A close-up photograph. Female contributor, age 18–29:
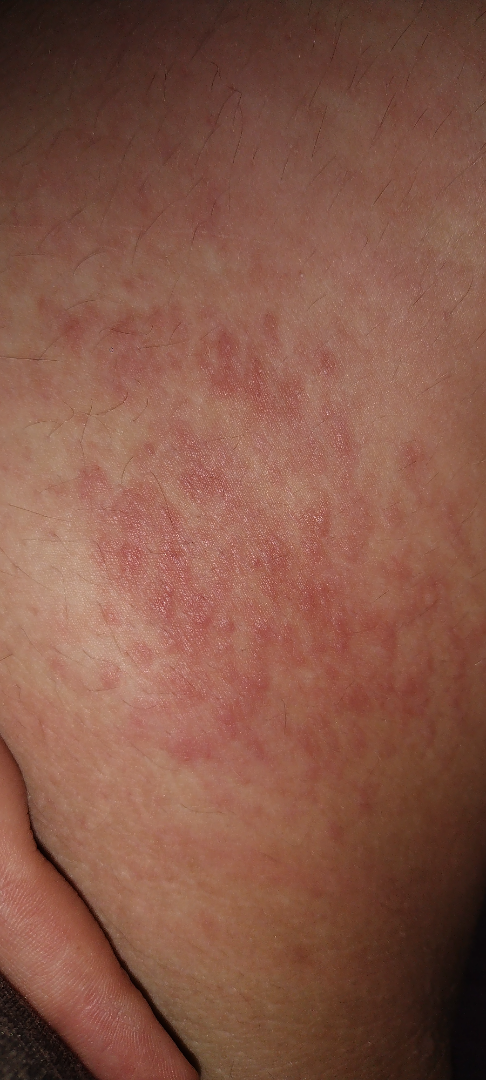differential — a single dermatologist reviewed the case: Eczema, Allergic Contact Dermatitis and Irritant Contact Dermatitis were considered with similar weight.